A dermatoscopic image of a skin lesion:
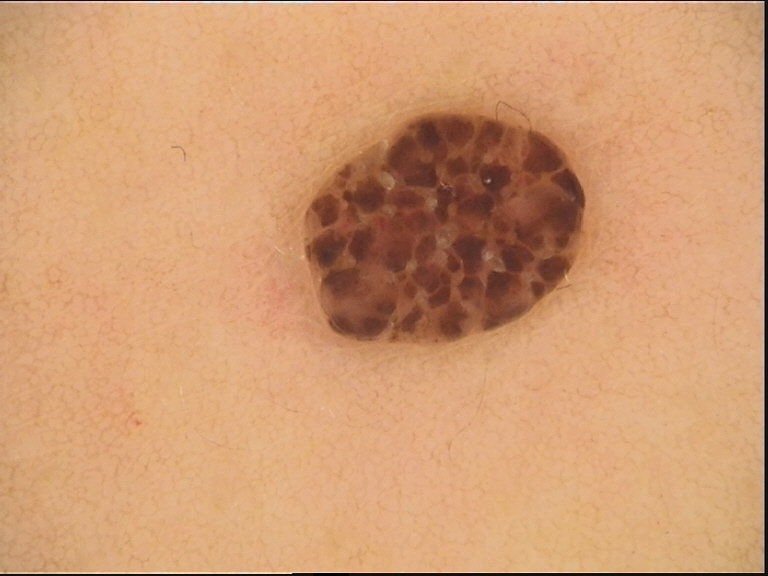Consistent with a banal lesion — a compound nevus.